A dermoscopic close-up of a skin lesion.
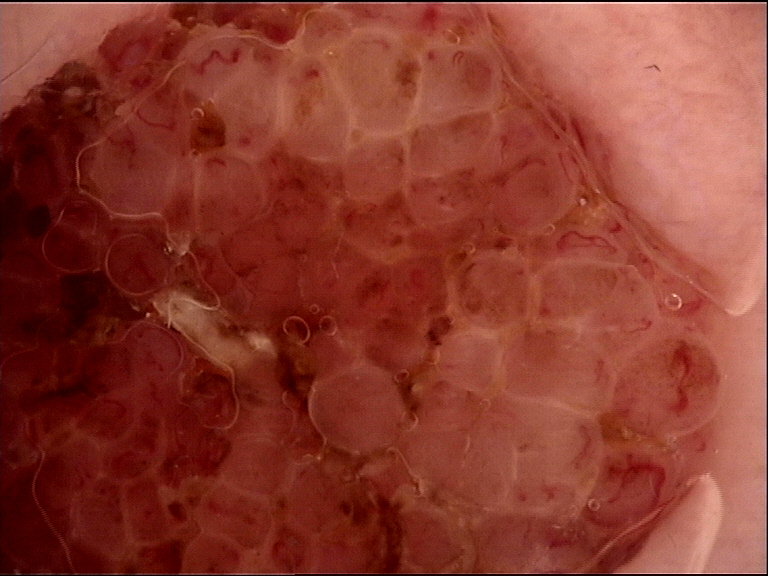Consistent with a banal lesion — a dermal nevus.